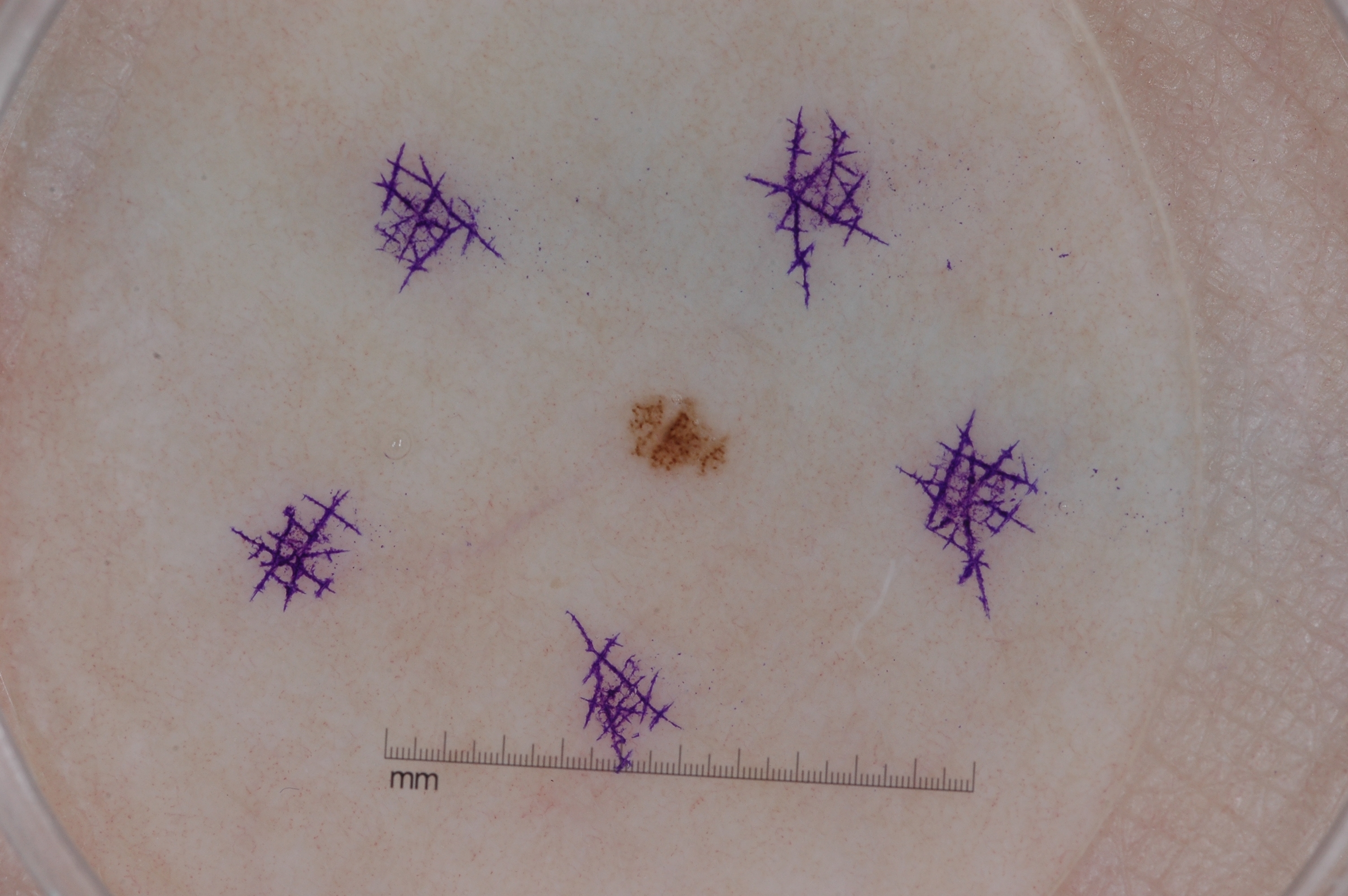A female patient, roughly 25 years of age. A skin lesion imaged with a dermatoscope. Dermoscopy demonstrates no streaks, pigment network, negative network, or milia-like cysts. With coordinates (x1, y1, x2, y2), the lesion spans 622/392/716/469. Expert review diagnosed this as a melanocytic nevus.